A dermoscopy image of a skin lesion; acquired for a research image collection, with no referral diagnosis; the patient says their skin tans without first burning; a male subject 72 years old: 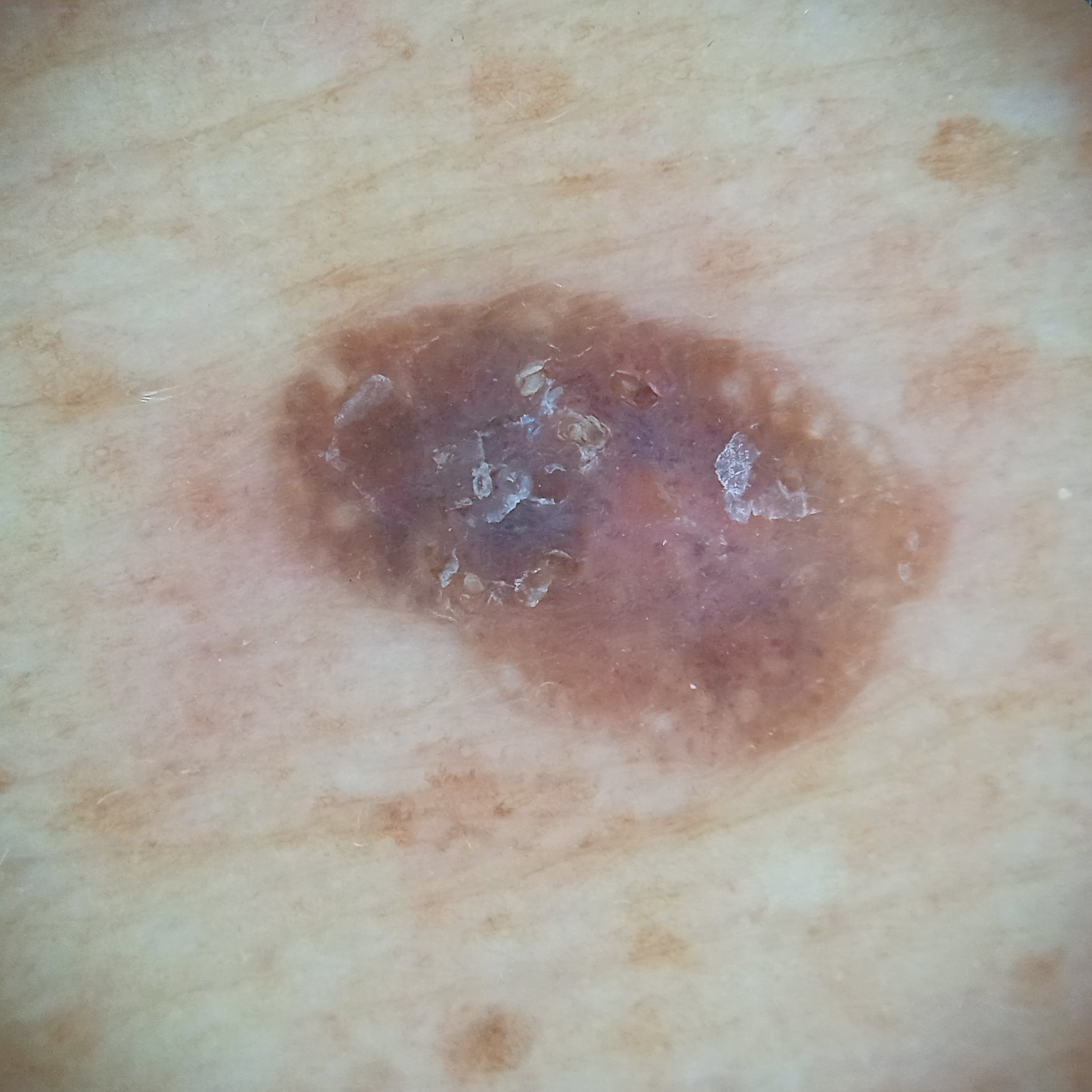size = 8.1 mm | assessment = seborrheic keratosis (dermatologist consensus).